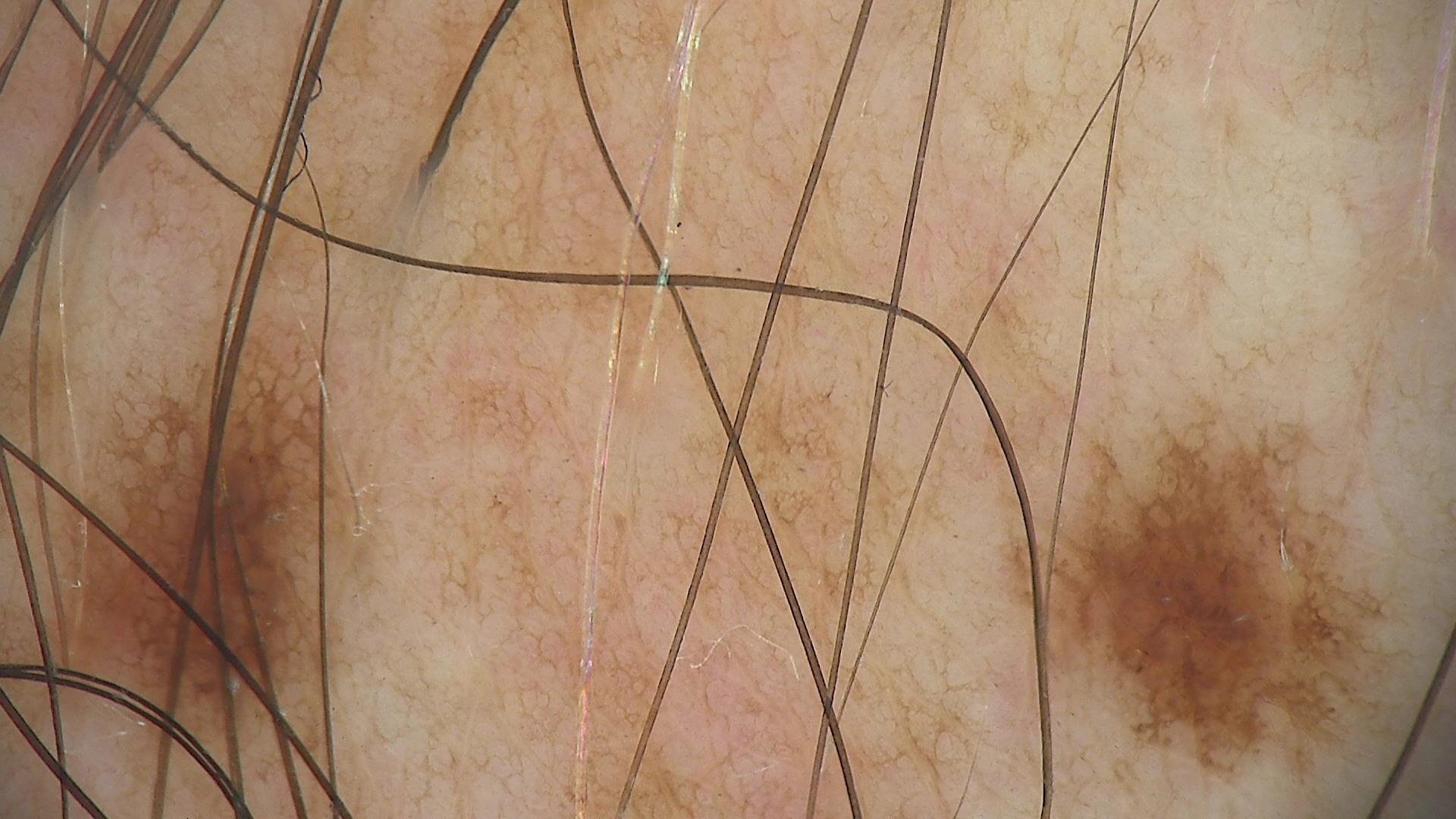image = dermoscopy; diagnostic label = dysplastic junctional nevus (expert consensus).